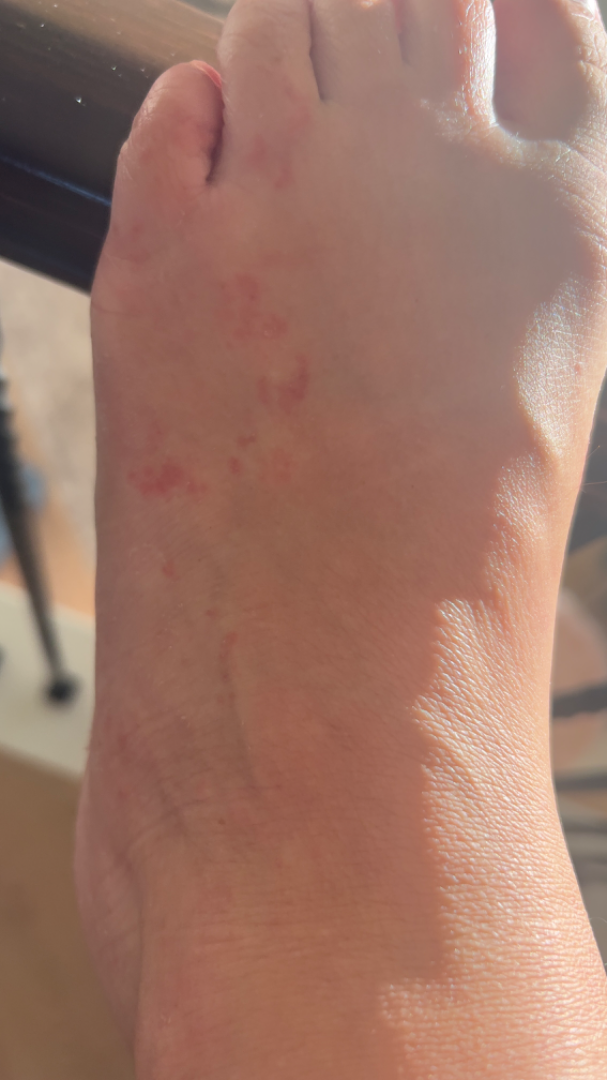differential diagnosis: Tinea and Cutaneous larva migrans were considered with similar weight; a remote consideration is Eczema.